A female patient 75 years of age; collected as part of a research study, without a referral diagnosis; the patient describes having a moderate number of moles.
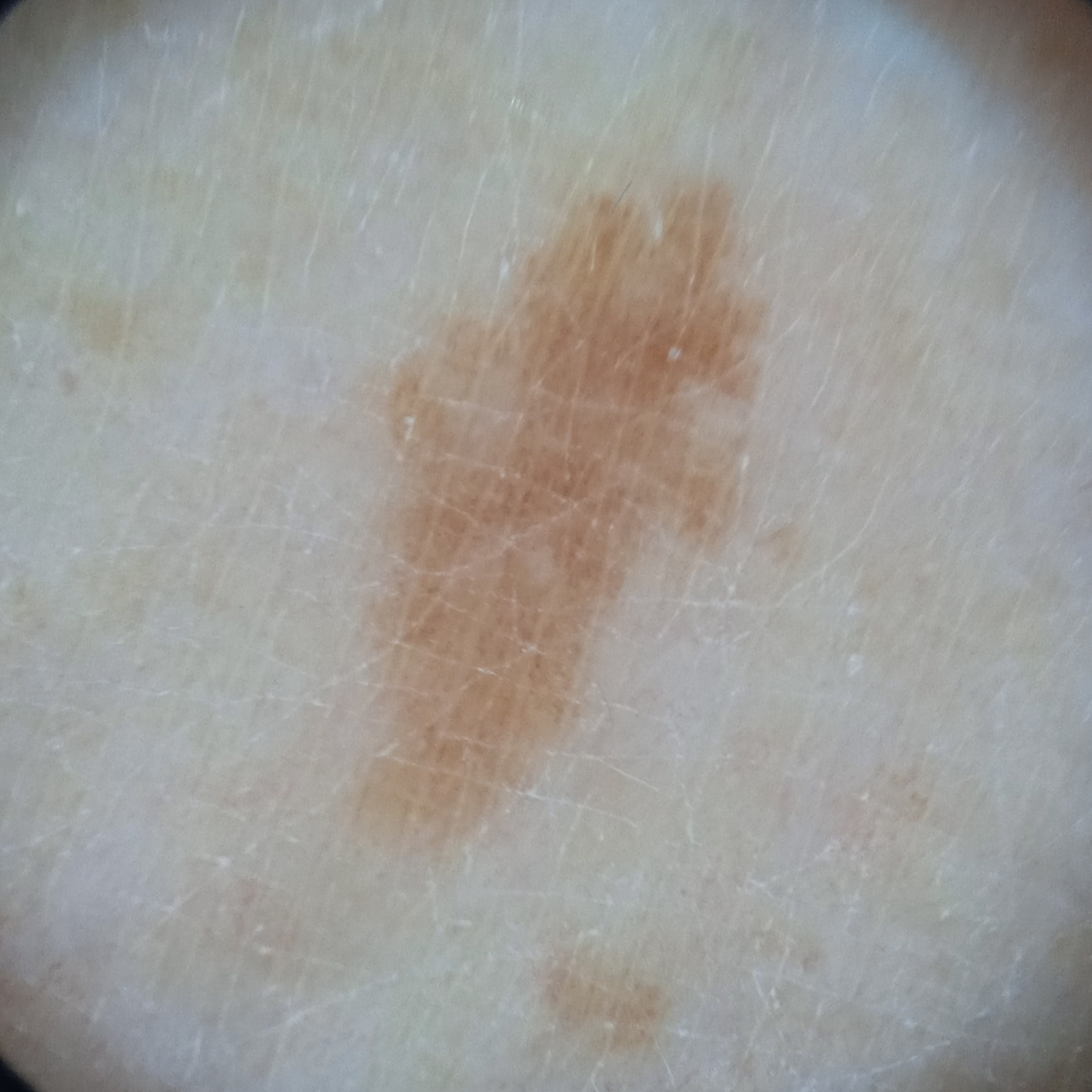<record>
  <lesion_location>a leg</lesion_location>
  <lesion_size>
    <diameter_mm>8.2</diameter_mm>
  </lesion_size>
  <diagnosis>
    <name>melanocytic nevus</name>
    <malignancy>benign</malignancy>
  </diagnosis>
</record>